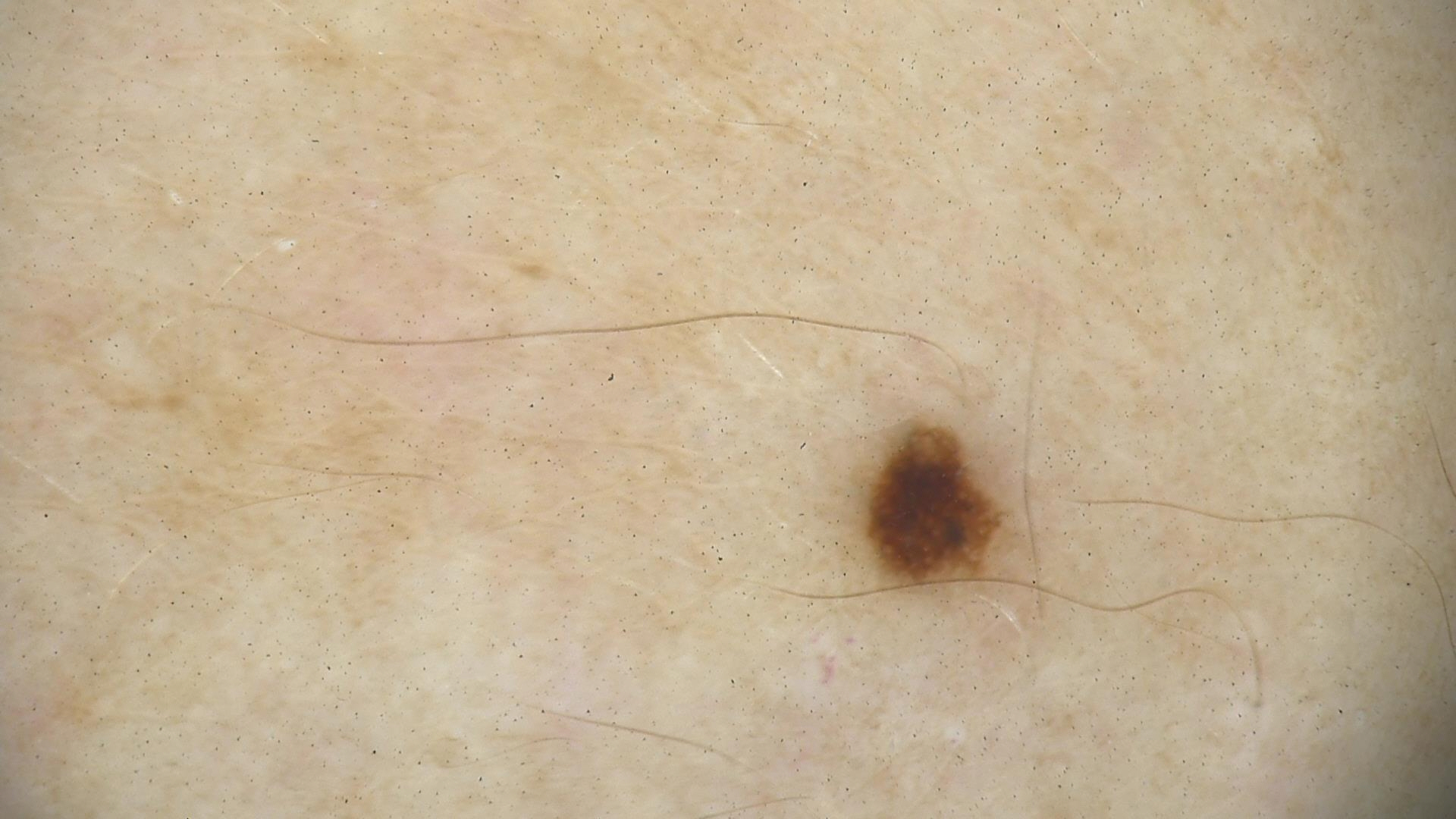The diagnostic label was a dysplastic junctional nevus.